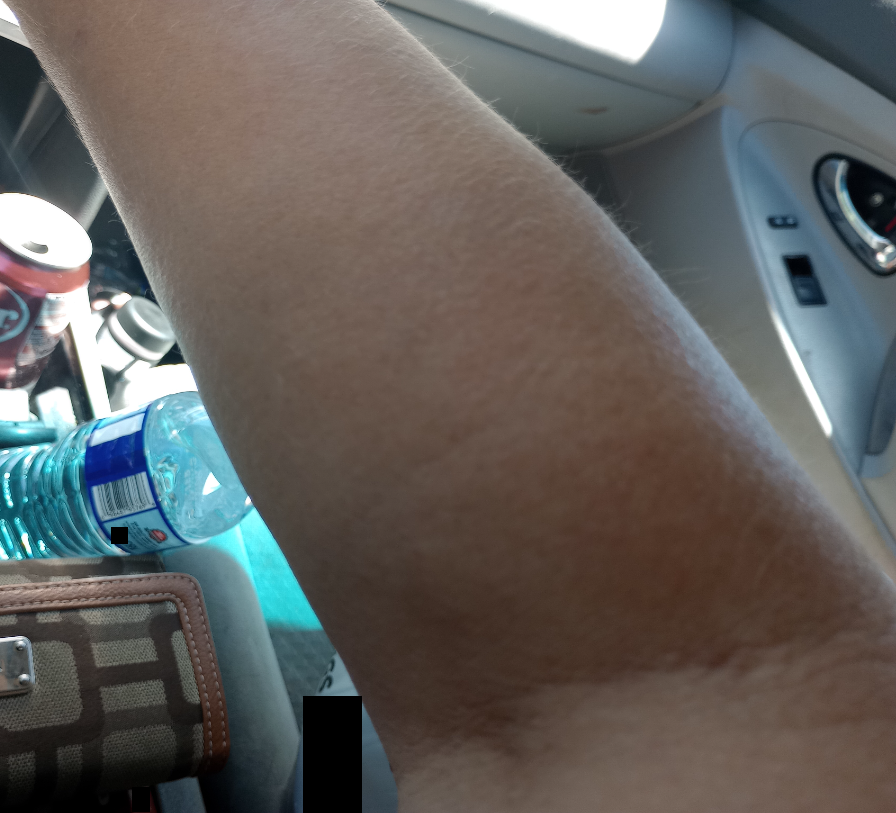The skin condition could not be confidently assessed from this image.